The condition has been present for less than one week · self-categorized by the patient as a rash · a close-up photograph · the affected area is the leg · reported lesion symptoms include burning, darkening, enlargement, itching and bothersome appearance — 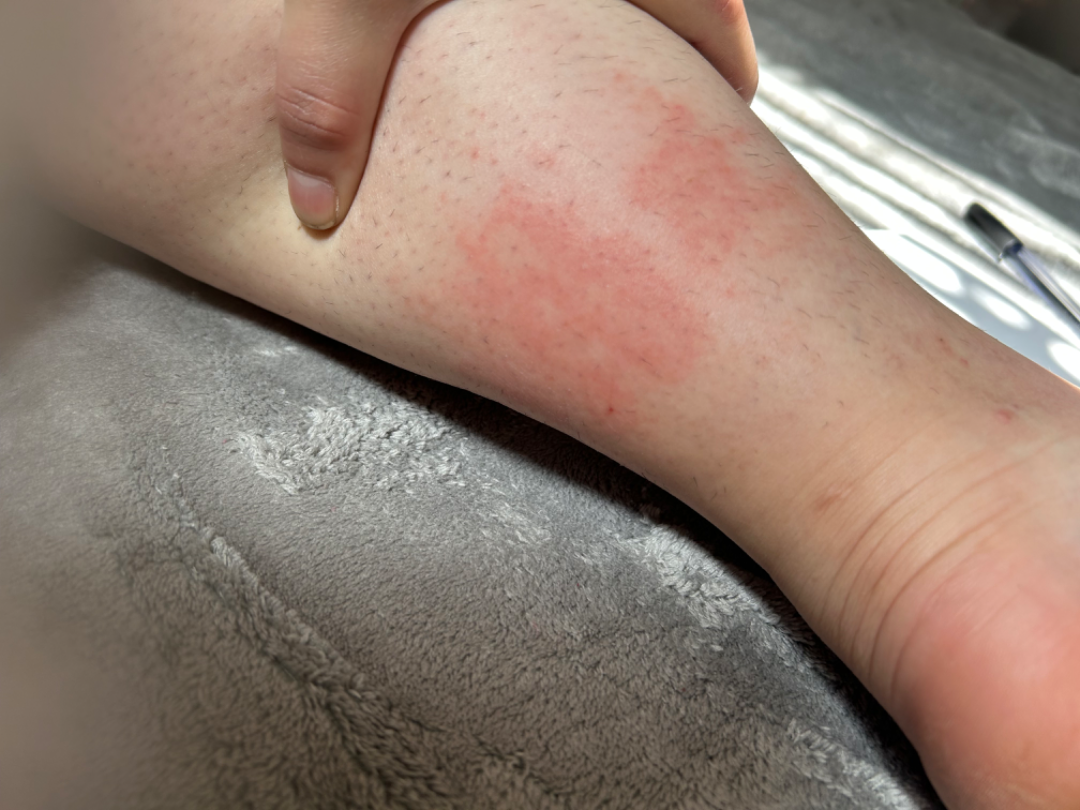impression: Urticaria and Eczema were each considered, in no particular order; a more distant consideration is Irritant Contact Dermatitis